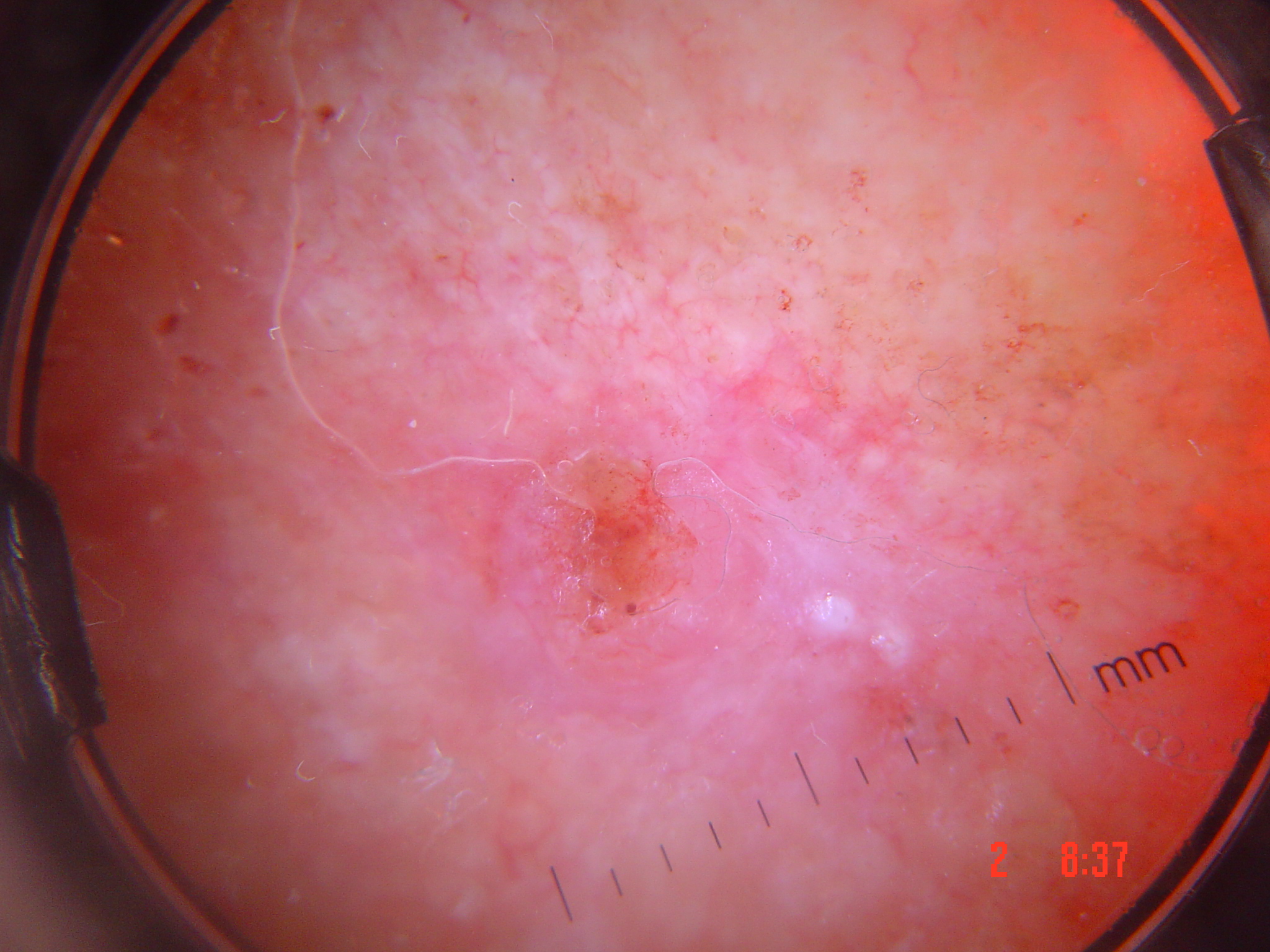The architecture is that of a keratinocytic lesion.
Histopathology confirmed a malignant lesion — a squamous cell carcinoma.